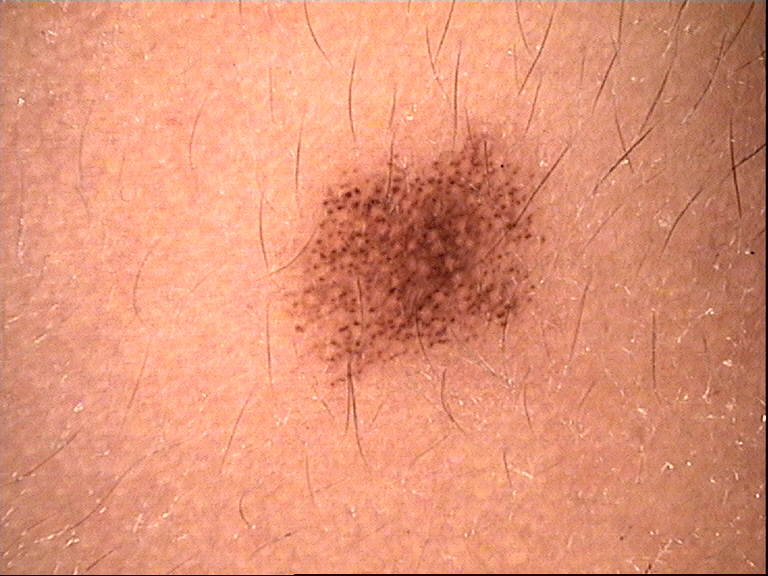  diagnosis:
    name: junctional nevus
    code: jb
    malignancy: benign
    super_class: melanocytic
    confirmation: expert consensus